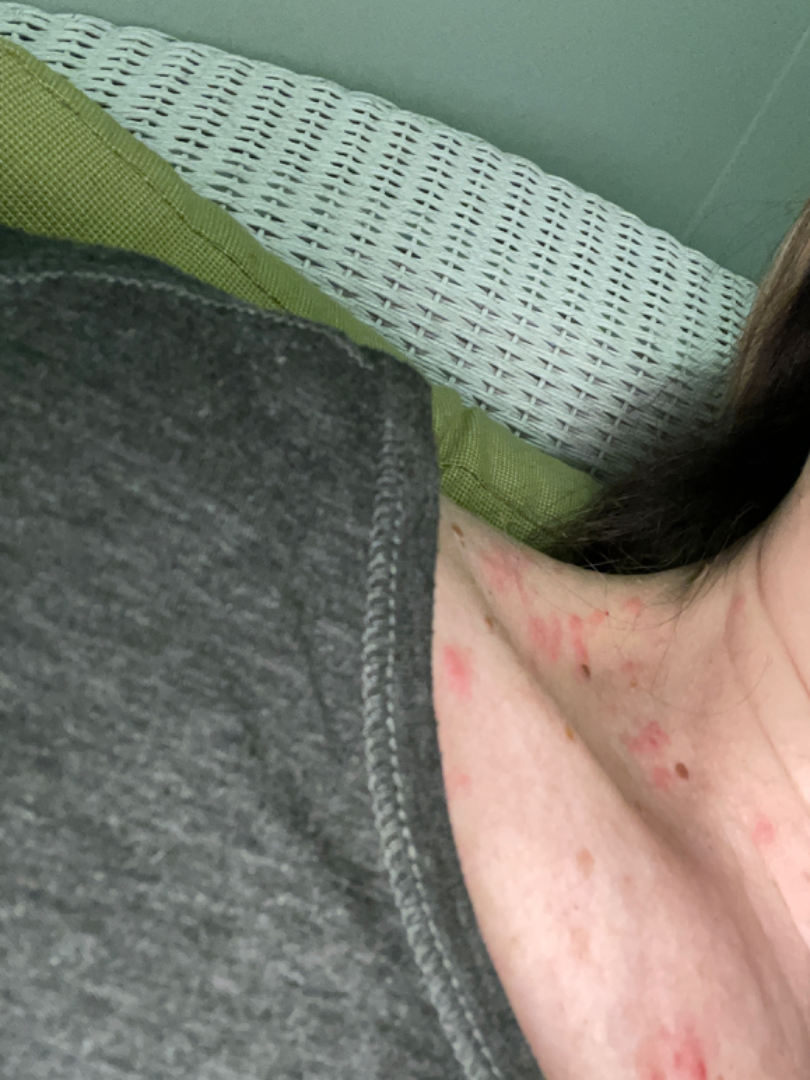assessment=not assessable; associated systemic symptoms=none reported; framing=close-up; texture=raised or bumpy; contributor=female, age 70–79; site=arm and head or neck.